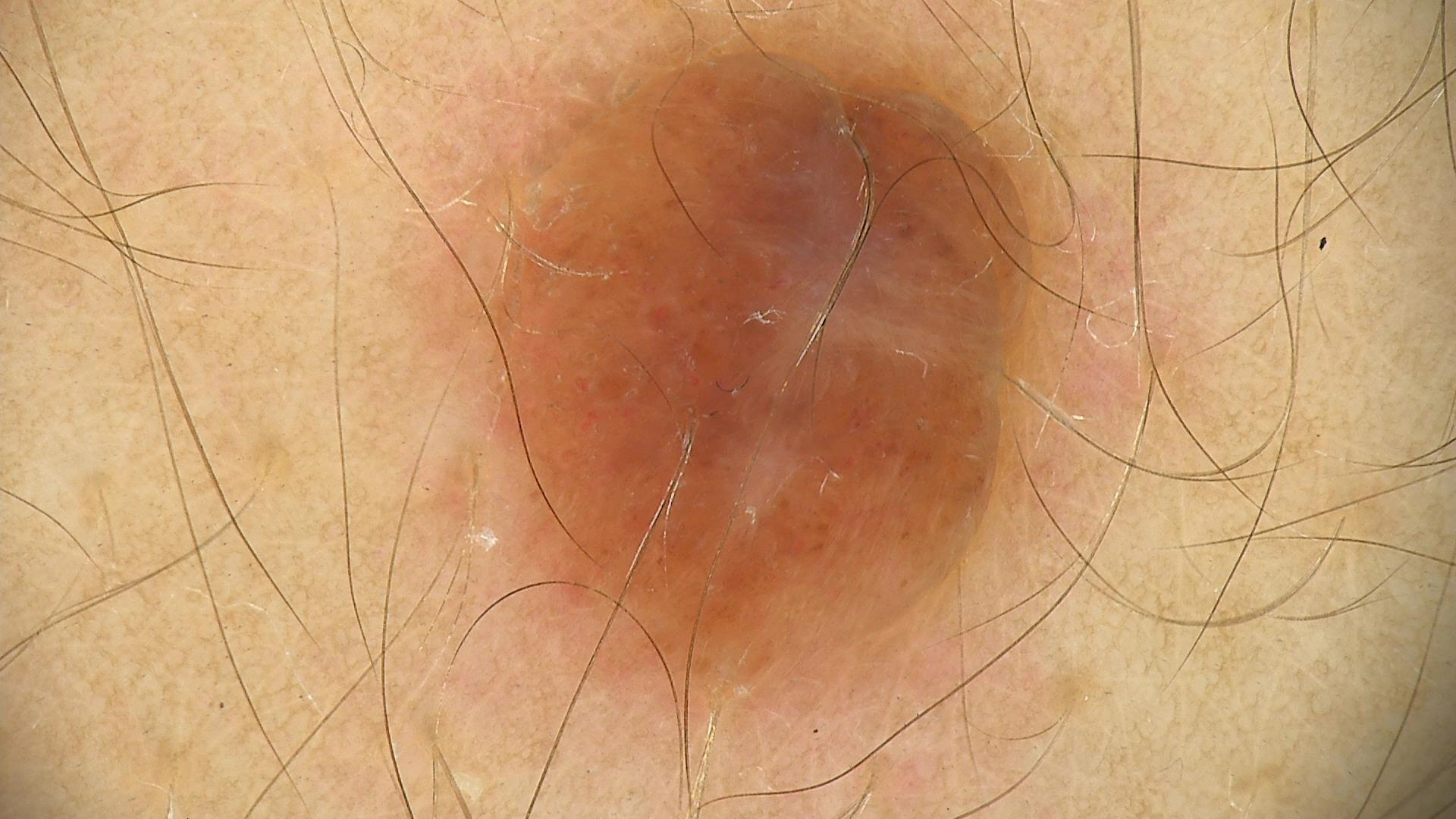The diagnostic label was a dermal nevus.